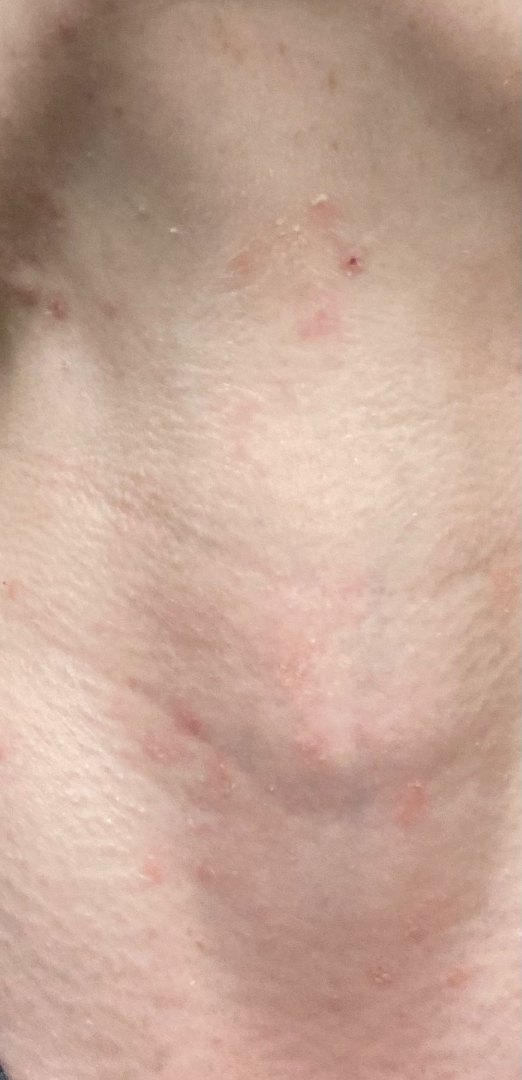Assessment:
The skin condition could not be confidently assessed from this image.
Clinical context:
Texture is reported as rough or flaky. Reported duration is one to three months. The photograph is a close-up of the affected area. The head or neck is involved. The contributor is 30–39, female.